This is a close-up image.
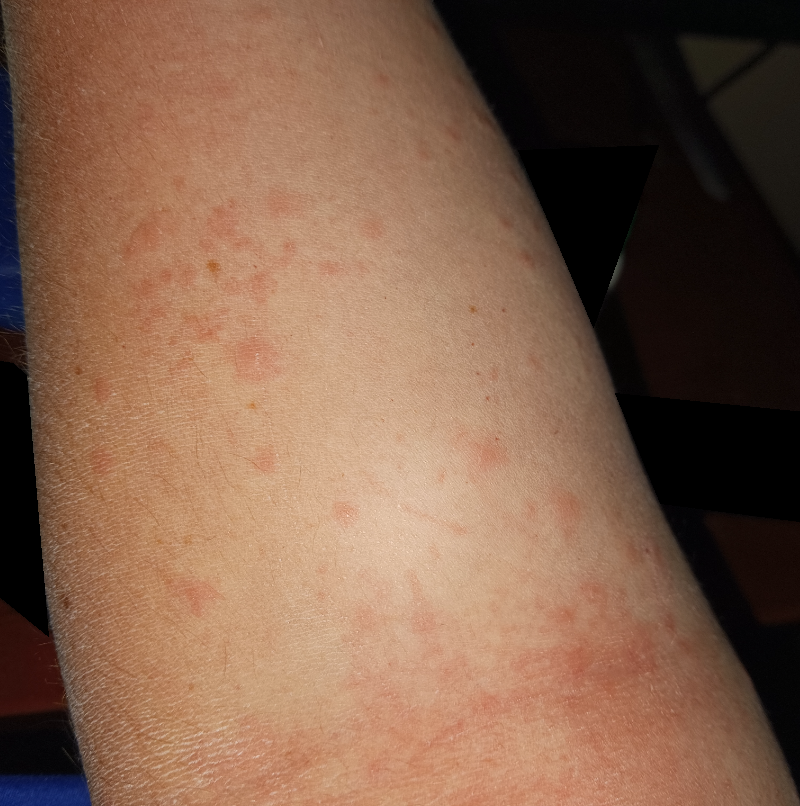Impression:
On remote review of the image: most consistent with Eczema.